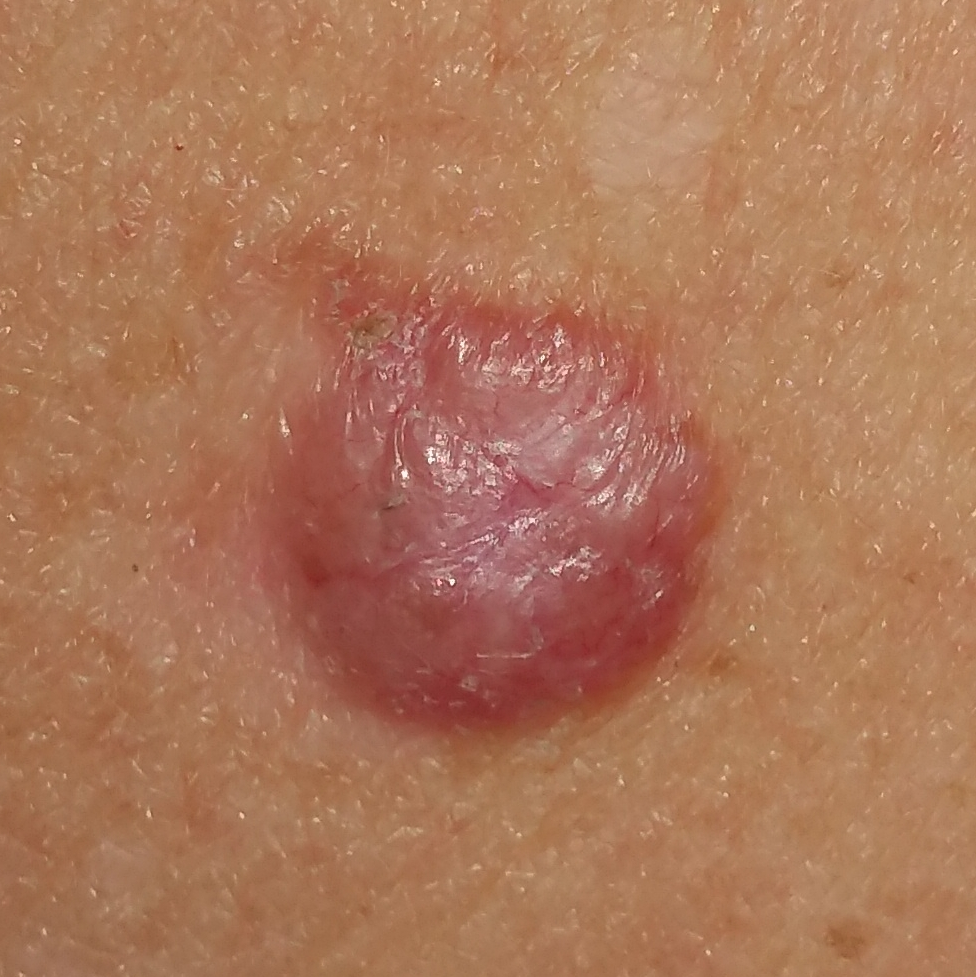A female subject in their early 70s. The lesion was found on the back. Per patient report, the lesion is elevated and itches. Confirmed on histopathology as a basal cell carcinoma.